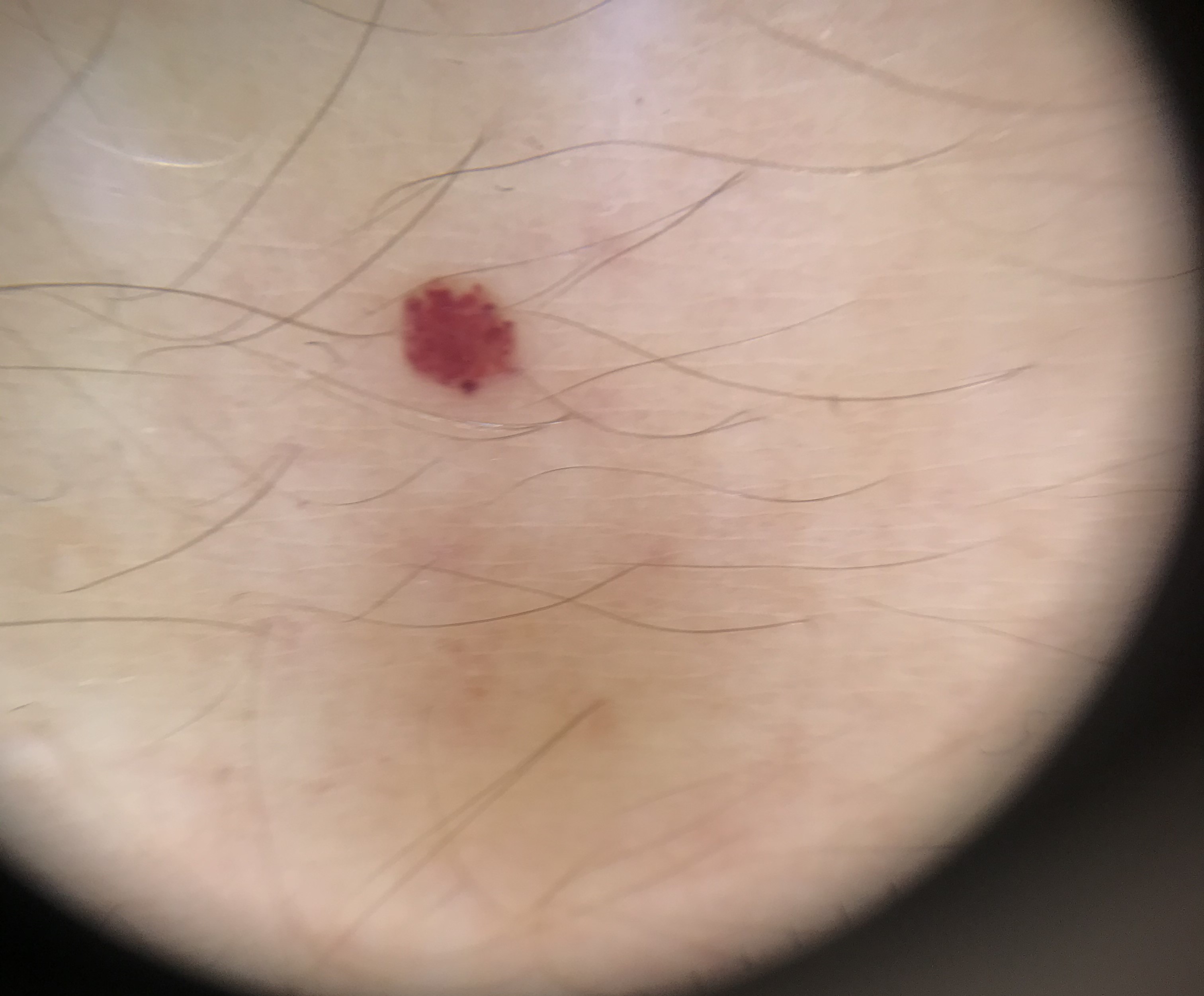Dermoscopy of a skin lesion. The morphology is that of a vascular lesion. Diagnosed as a benign lesion — a hemangioma.